The condition has been present for one to four weeks, no relevant systemic symptoms, the subject is a female aged 70–79, the contributor notes the lesion is raised or bumpy, located on the leg, the photo was captured at a distance, reported lesion symptoms include bothersome appearance, the patient considered this a rash:
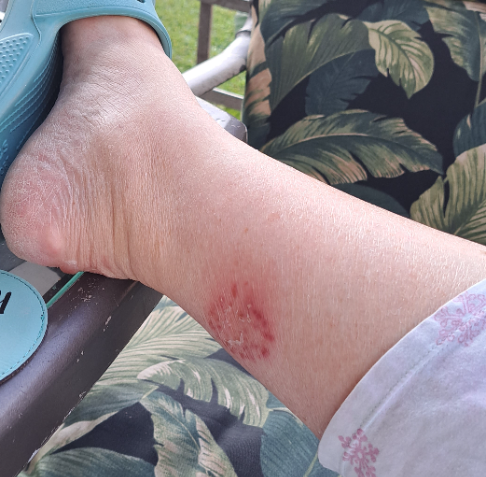Review: Eczema (100%).